By history, tobacco use, pesticide exposure, alcohol use, and no prior malignancy (patient or family). Recorded as FST II. A male patient age 51. A smartphone photograph of a skin lesion:
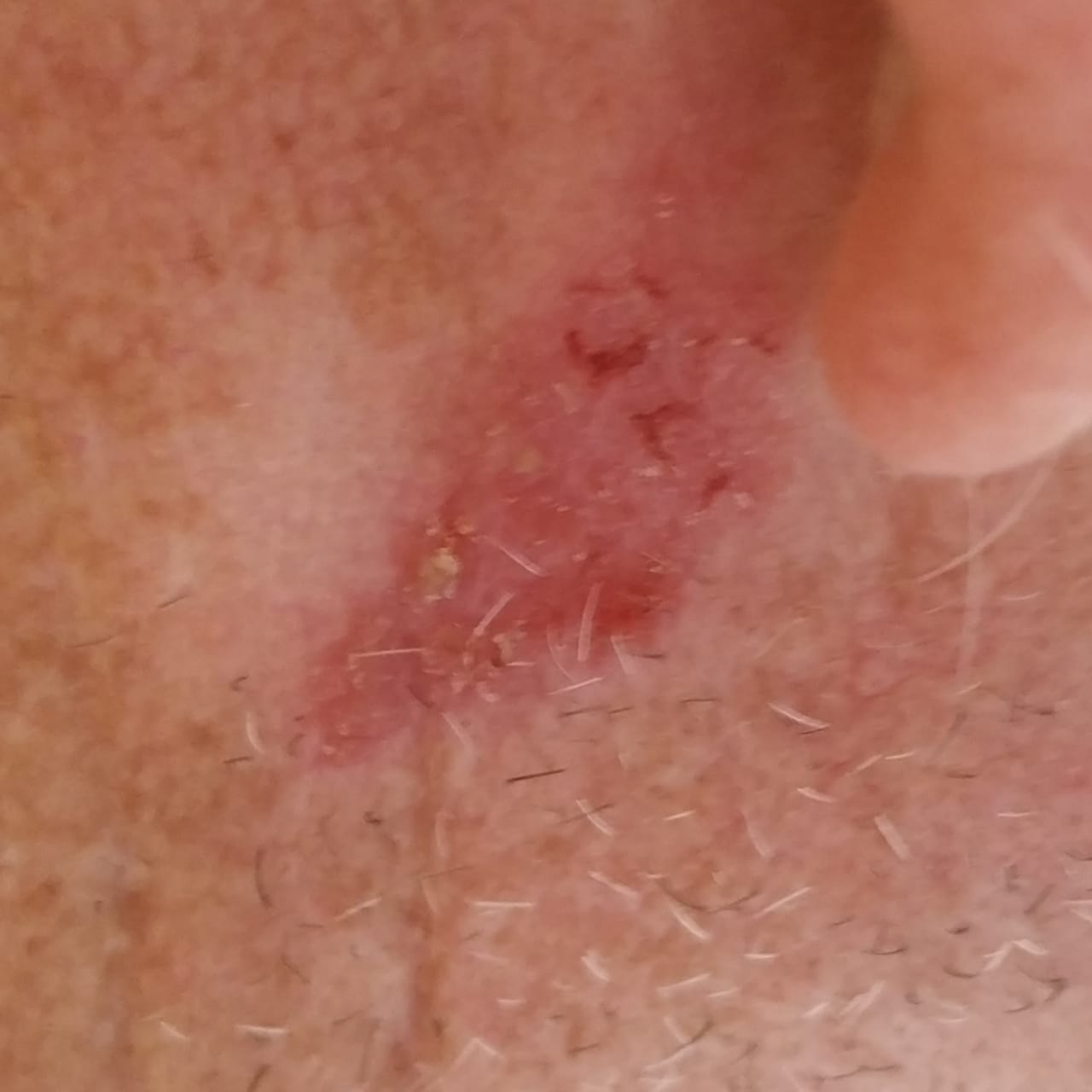The lesion is located on an ear. Measuring about 15 × 13 mm. The biopsy diagnosis was a basal cell carcinoma.